A male subject aged approximately 80; an overview clinical photograph of a skin lesion.
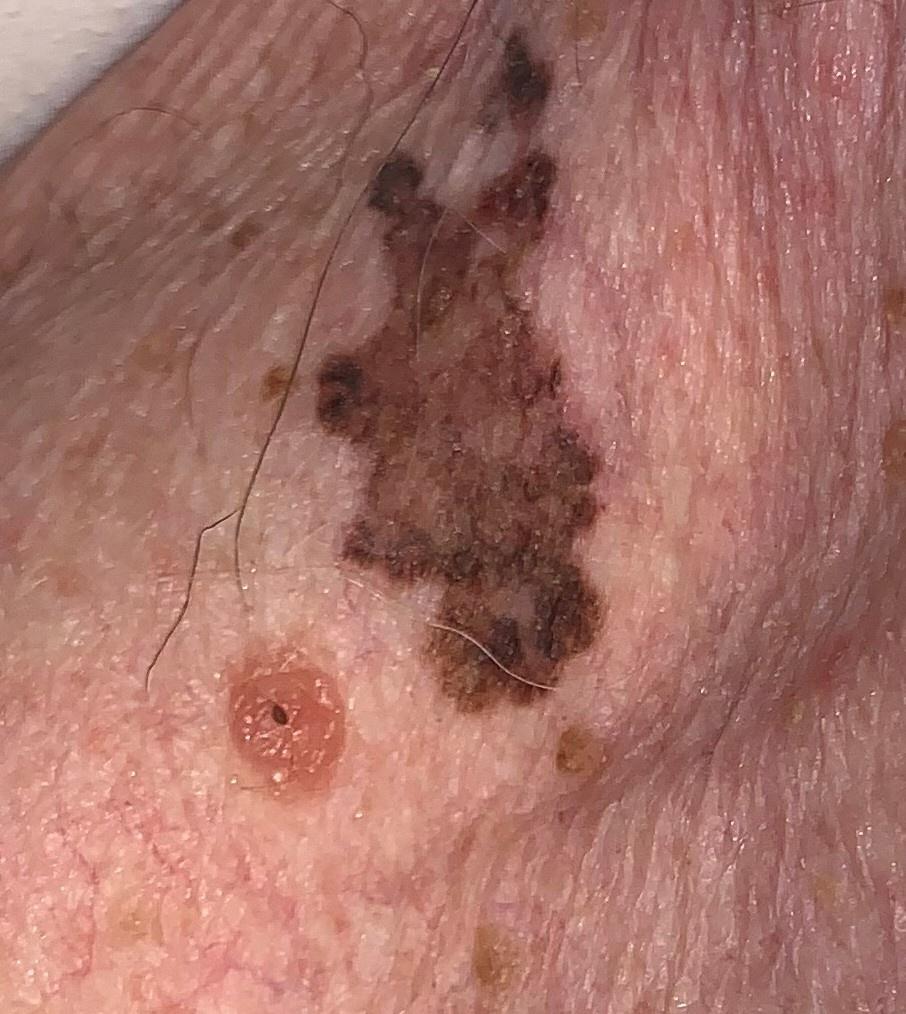site: the trunk, specifically the anterior trunk; diagnosis: Melanoma (biopsy-proven).